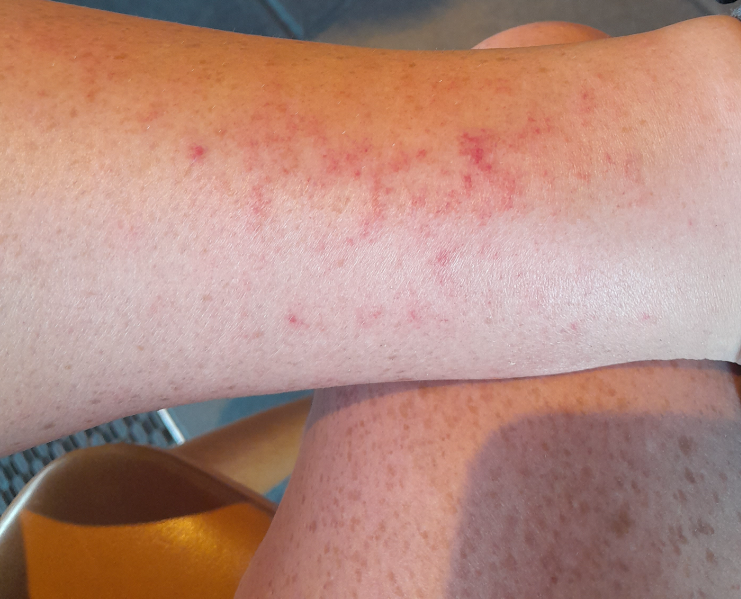Present for less than one week.
The patient described the issue as a rash.
The contributor notes bothersome appearance.
Fitzpatrick skin type II; lay reviewers estimated Monk skin tone scale 2 or 3 (two reviewer pools).
The lesion involves the leg.
Close-up view.
The lesion is described as flat.
The contributor is 30–39, female.
The differential, in no particular order, includes Pigmented purpuric eruption, Eczema and Leukocytoclastic Vasculitis.